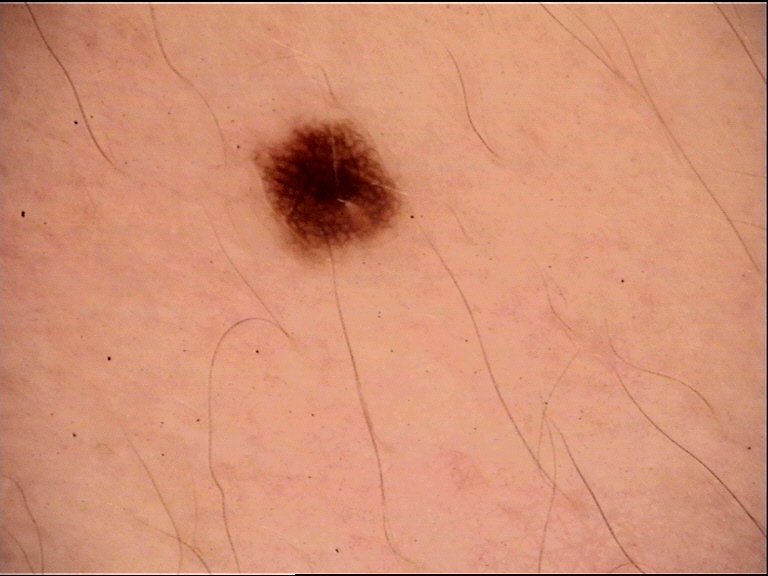{
  "image": "dermoscopy",
  "diagnosis": {
    "name": "dysplastic junctional nevus",
    "code": "jd",
    "malignancy": "benign",
    "super_class": "melanocytic",
    "confirmation": "expert consensus"
  }
}